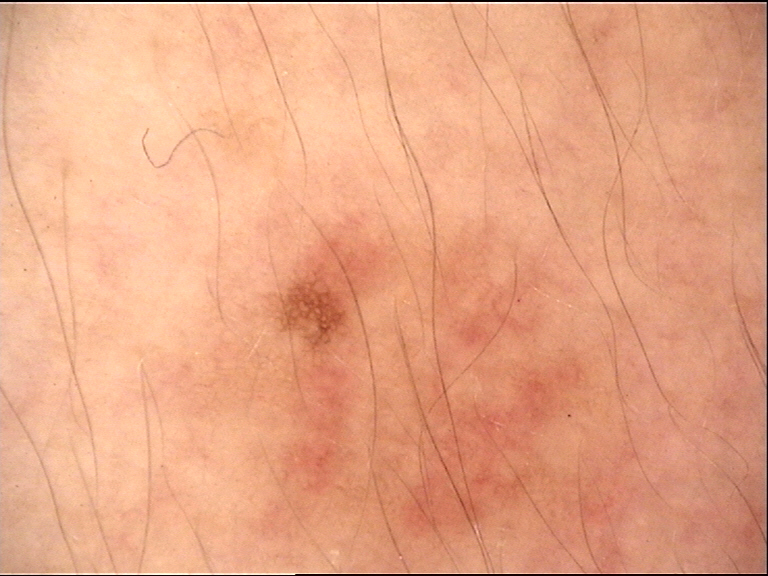Findings:
A skin lesion imaged with a dermatoscope.
Impression:
Diagnosed as a dysplastic junctional nevus.